A dermoscopic photograph of a skin lesion:
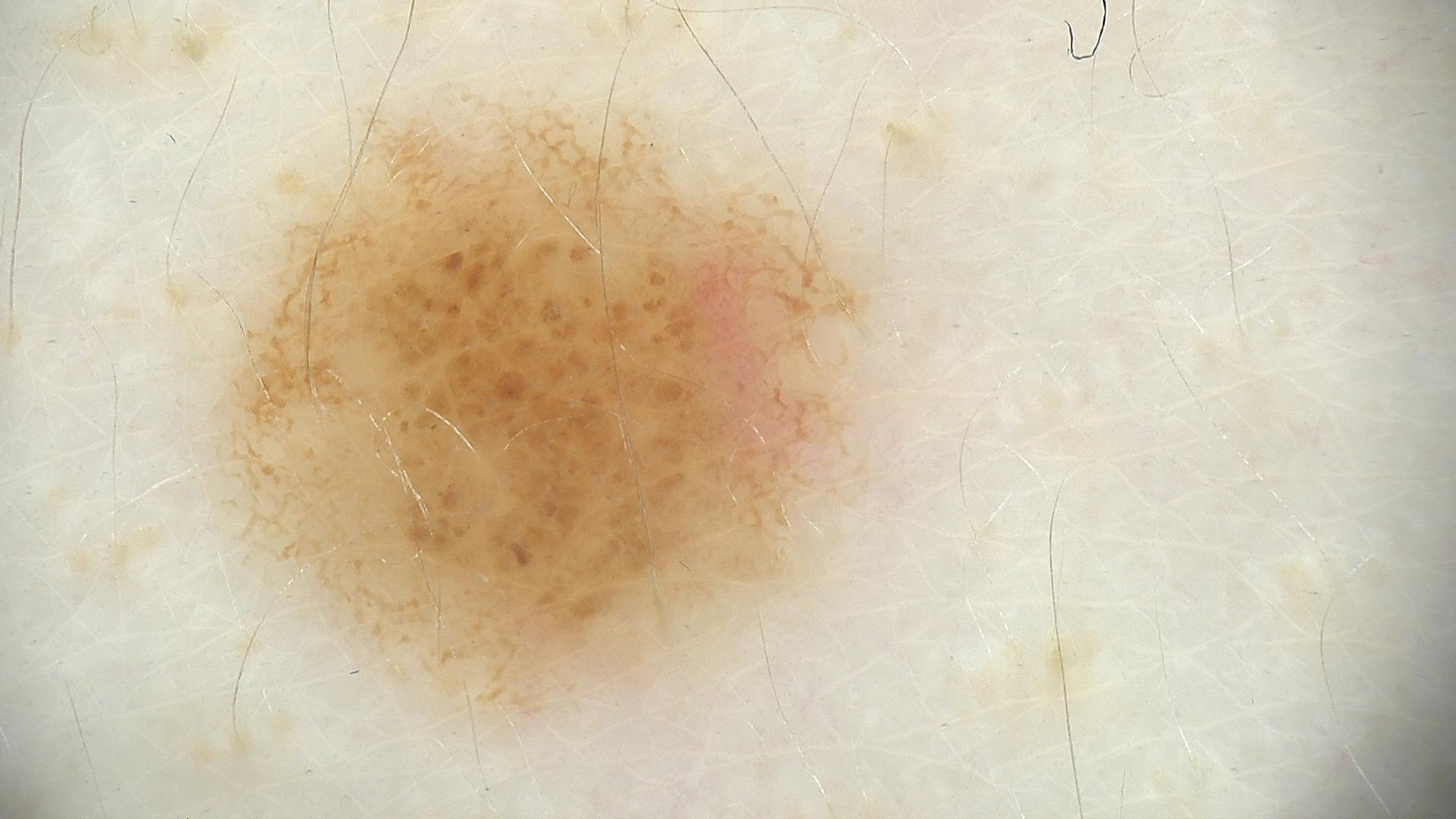The diagnostic label was a dysplastic junctional nevus.